The photo was captured at a distance. The lesion involves the leg. Male contributor, age 40–49 — 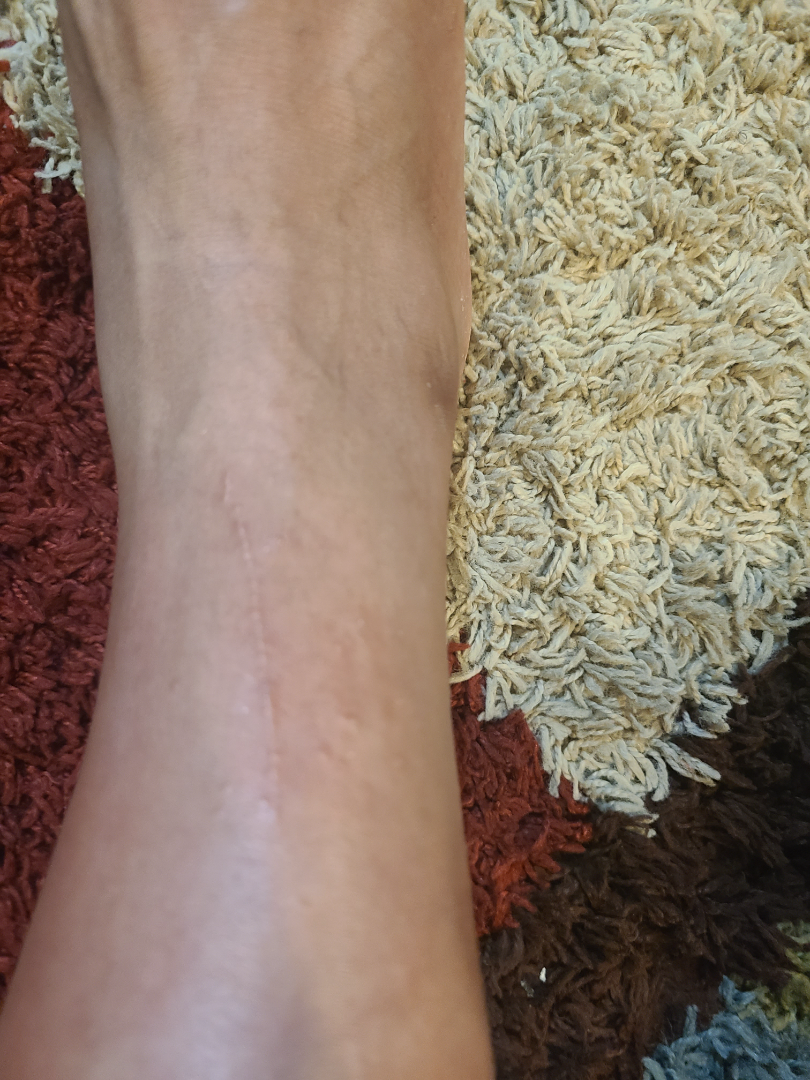Background: Texture is reported as raised or bumpy. The contributor notes the condition has been present for one to four weeks. Symptoms reported: itching. Findings: On dermatologist assessment of the image: Lichen planus/lichenoid eruption, Koebner phenomenon and Allergic Contact Dermatitis were each considered, in no particular order; less probable is Lichen nitidus; a more distant consideration is Verruca vulgaris.